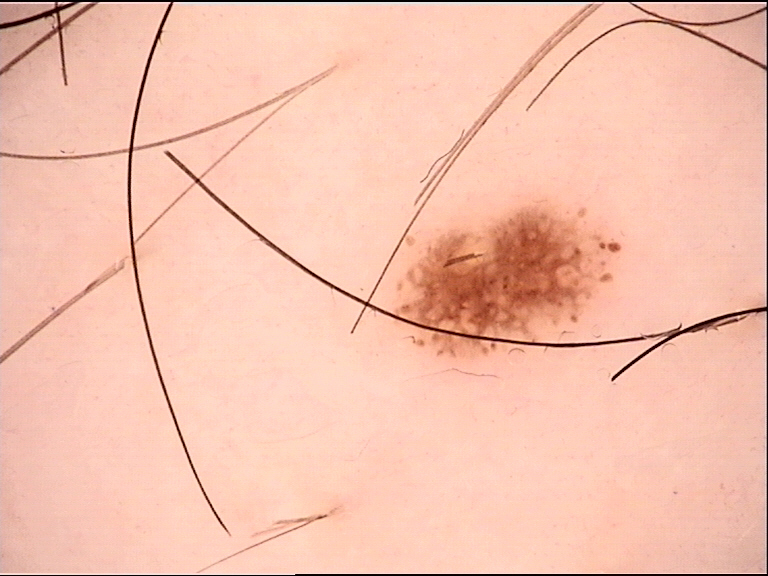The diagnosis was a dysplastic junctional nevus.